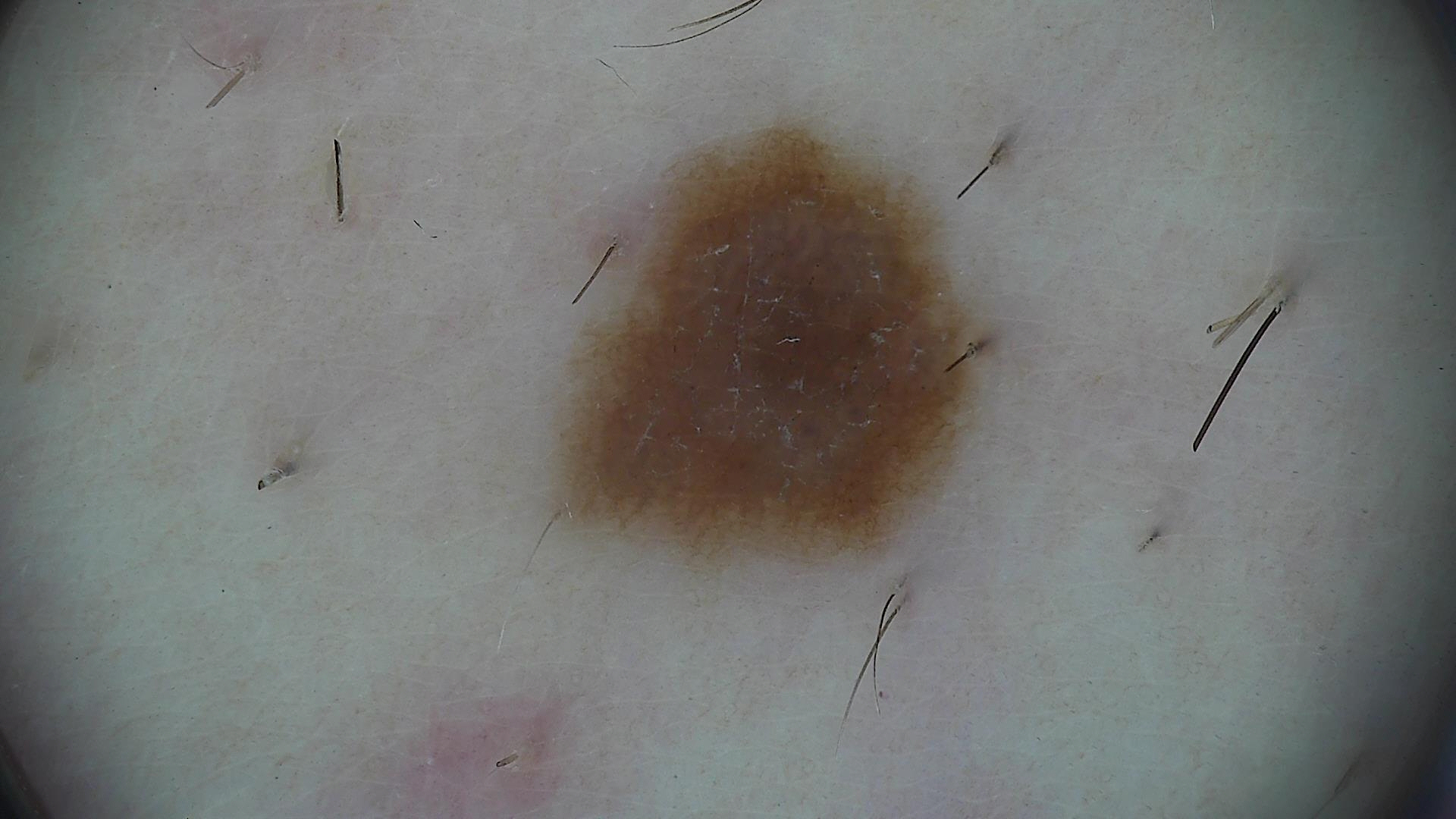A dermatoscopic image of a skin lesion. Labeled as a dysplastic junctional nevus.